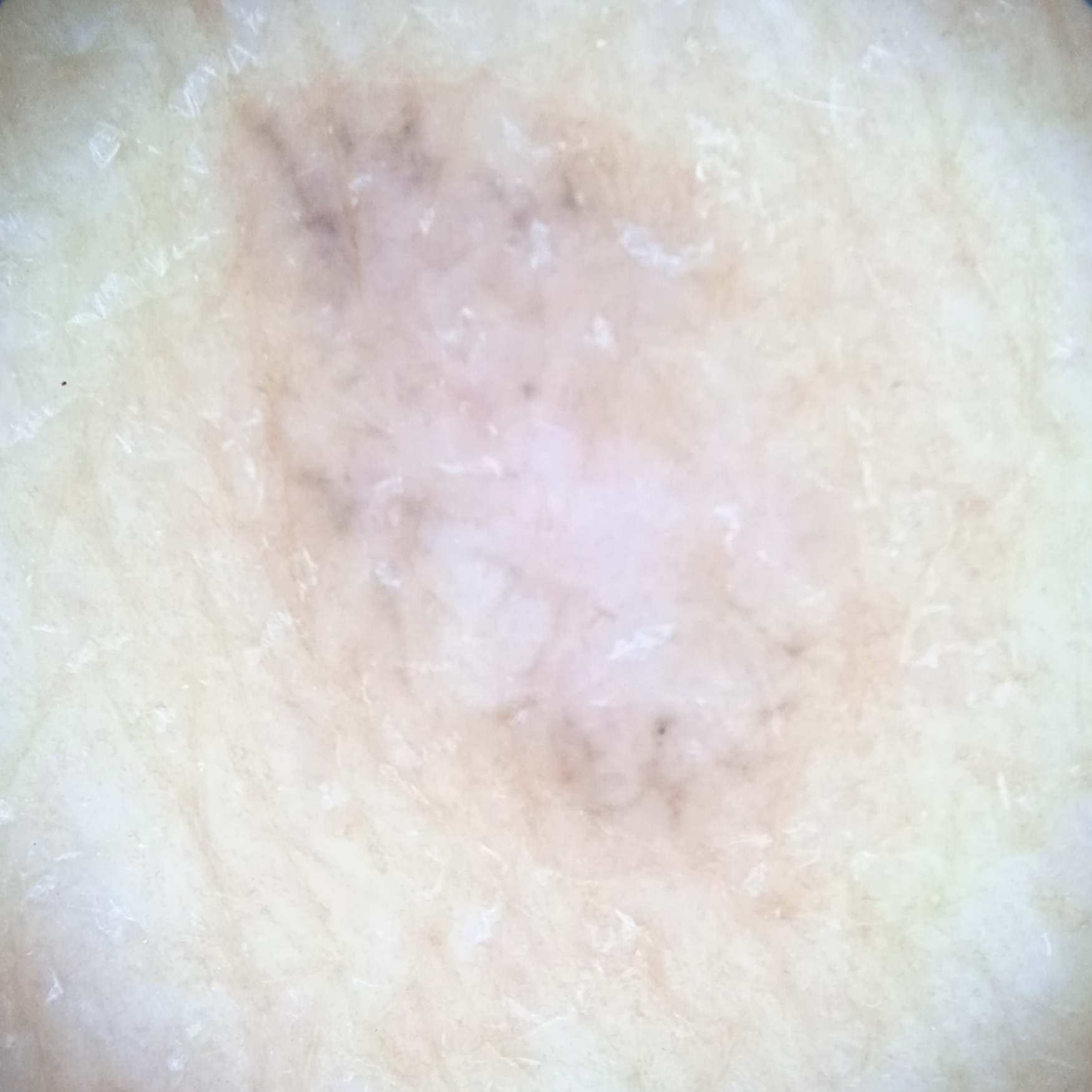A skin lesion imaged with a dermatoscope.
The patient says their skin tans without first burning.
By self-report, a personal history of cancer and a personal history of skin cancer.
The lesion is located on the back.
Measuring roughly 10.4 mm.
The dermatologists' assessment was a basal cell carcinoma.